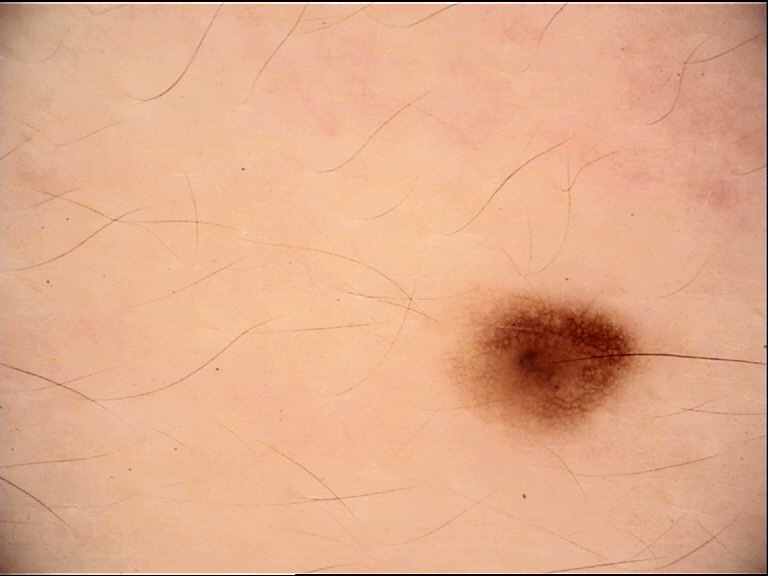image: dermoscopy, diagnostic label: compound nevus (expert consensus).